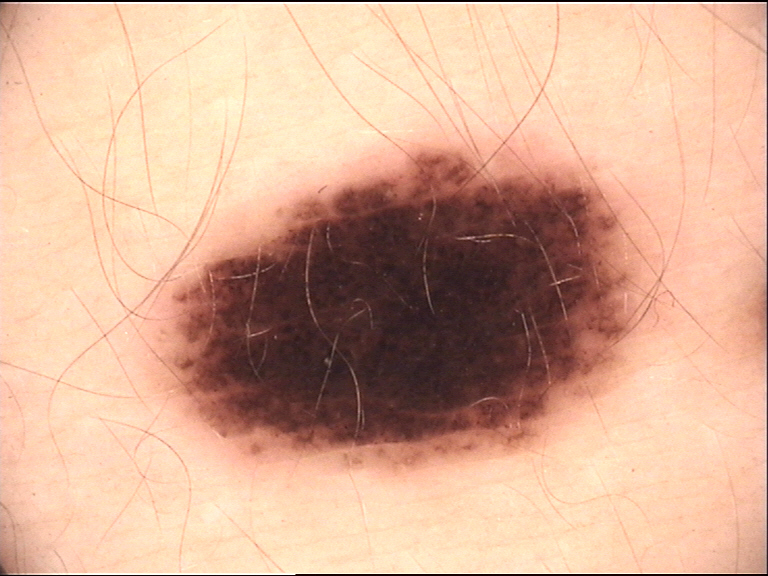  image: dermoscopy
  diagnosis:
    name: dysplastic compound nevus
    code: cd
    malignancy: benign
    super_class: melanocytic
    confirmation: expert consensus